Few moles overall by the patient's own estimate. Collected as part of a research study, without a referral diagnosis. By self-report, a family history of skin cancer and a history of sunbed use.
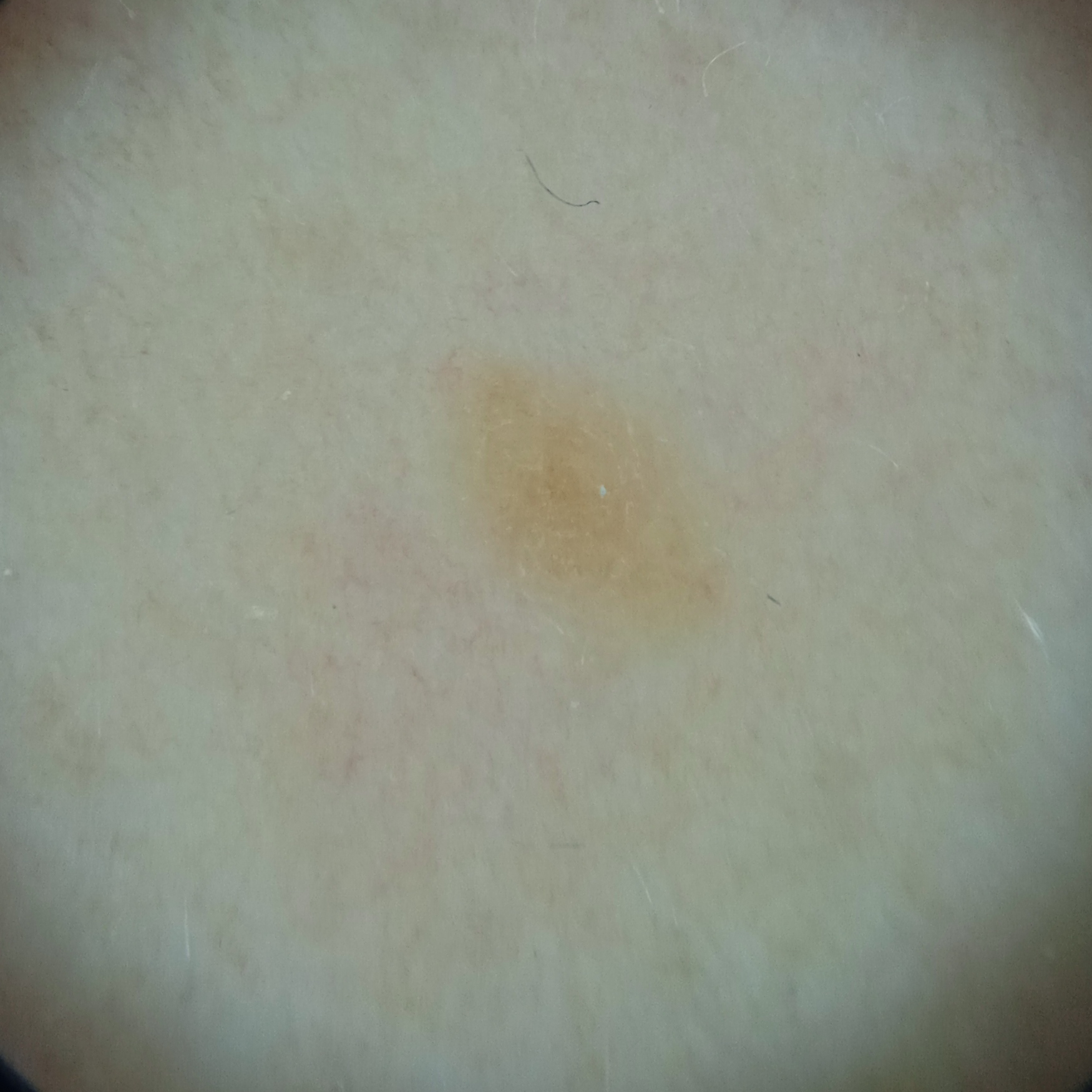site: the back
lesion size: 3.8 mm
assessment: seborrheic keratosis (dermatologist consensus)